A skin lesion imaged with a dermatoscope: 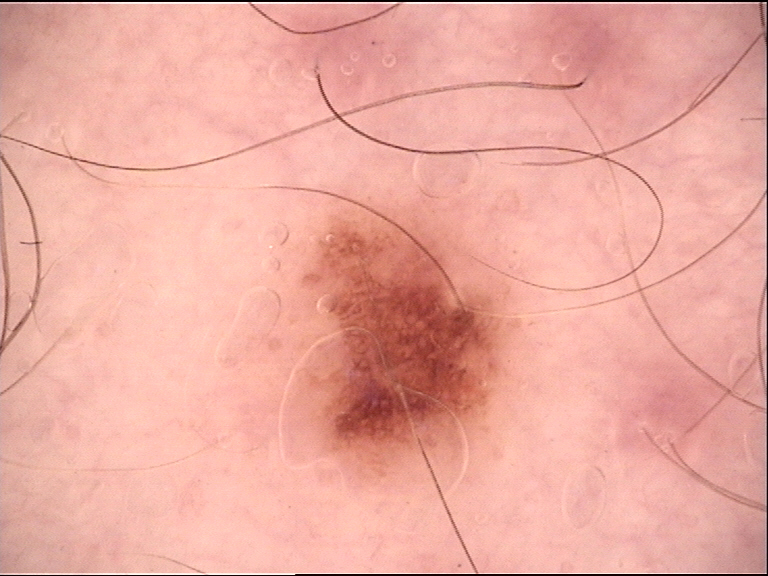diagnostic label: dysplastic junctional nevus (expert consensus).